Dermoscopy of a skin lesion: 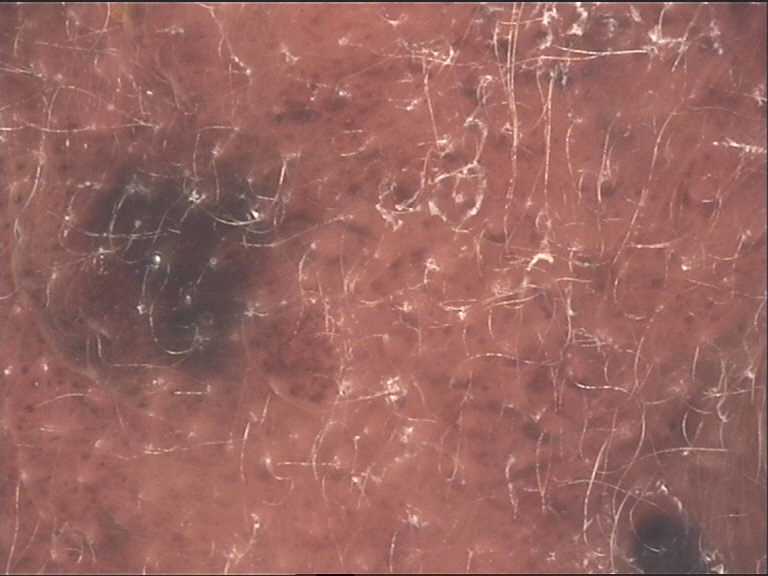Q: How is the lesion classified?
A: banal
Q: What is this lesion?
A: congenital compound nevus (expert consensus)